This image was taken at a distance; the lesion involves the back of the hand:
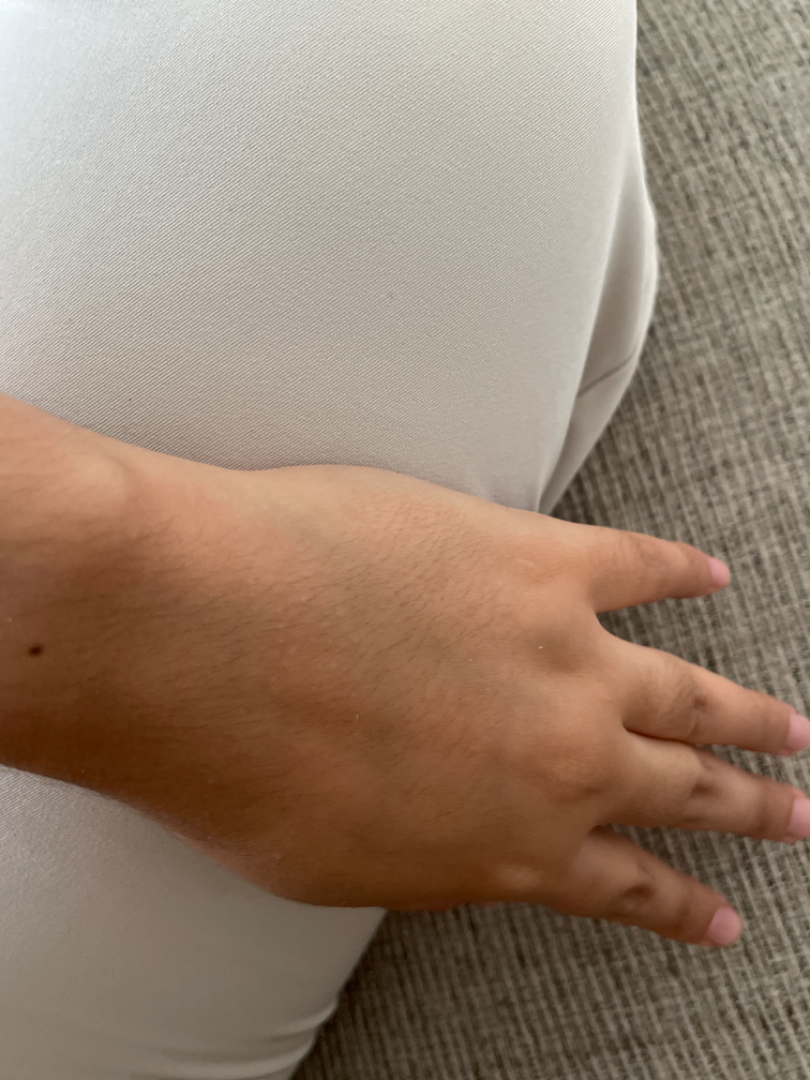The skin condition could not be confidently assessed from this image.